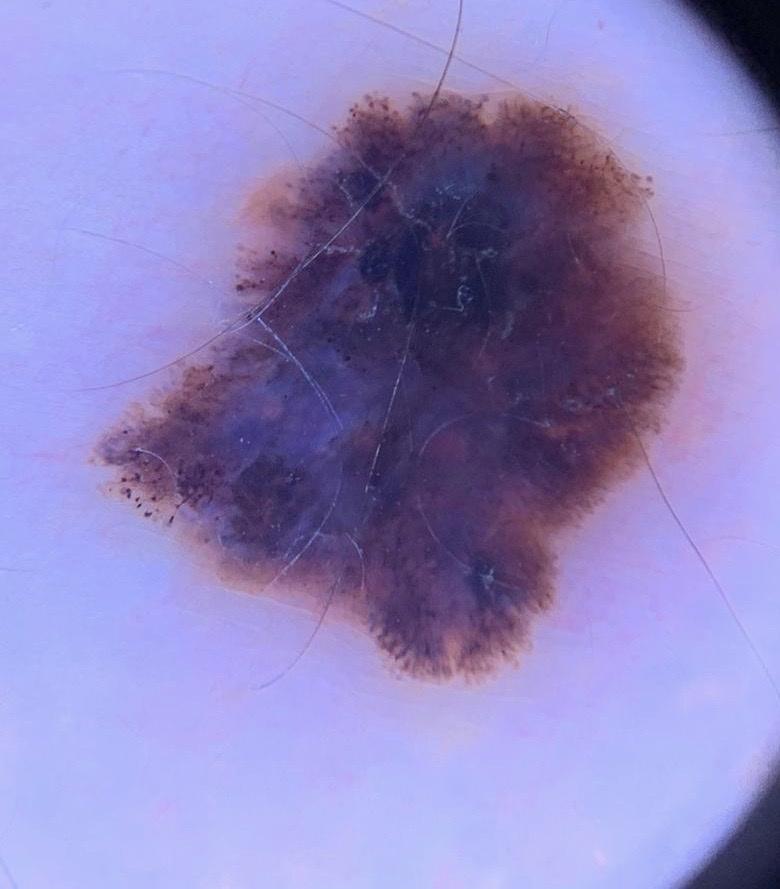Q: What Fitzpatrick skin type was recorded?
A: II
Q: How was this image acquired?
A: dermoscopy
Q: What are the patient's age and sex?
A: male, aged around 40
Q: Any relevant melanoma history?
A: a prior melanoma and melanoma in a first-degree relative
Q: What is the anatomic site?
A: the trunk, specifically the posterior trunk
Q: What is the diagnosis?
A: Melanoma (biopsy-proven)